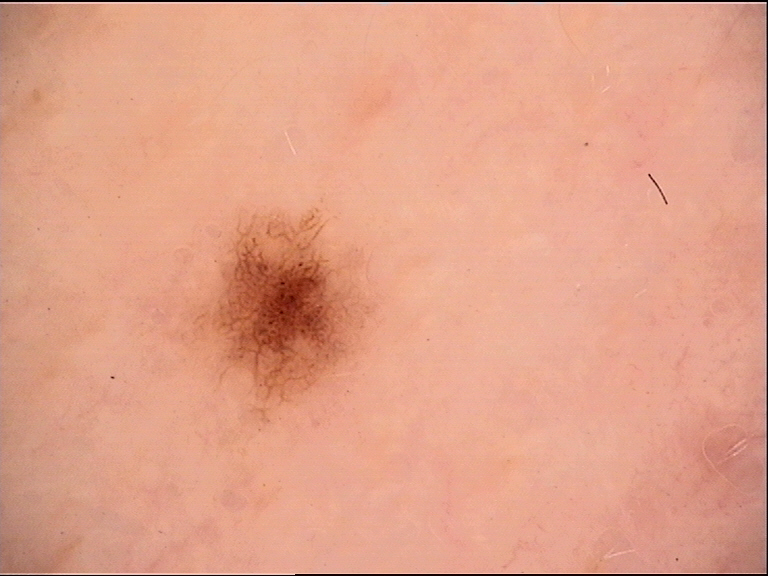Summary: Dermoscopy of a skin lesion. Impression: The diagnosis was a benign lesion — a dysplastic junctional nevus.